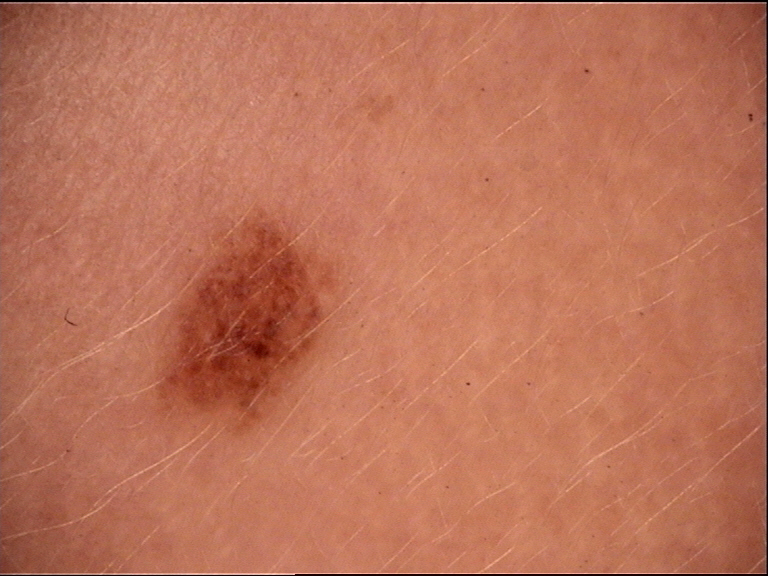| field | value |
|---|---|
| diagnosis | dysplastic junctional nevus (expert consensus) |